Male patient, age 50–59. The patient considered this skin that appeared healthy to them. The patient did not report lesion symptoms. The affected area is the leg. The lesion is described as raised or bumpy. An image taken at a distance. The contributor reports the condition has been present for less than one week. The patient also reports joint pain:
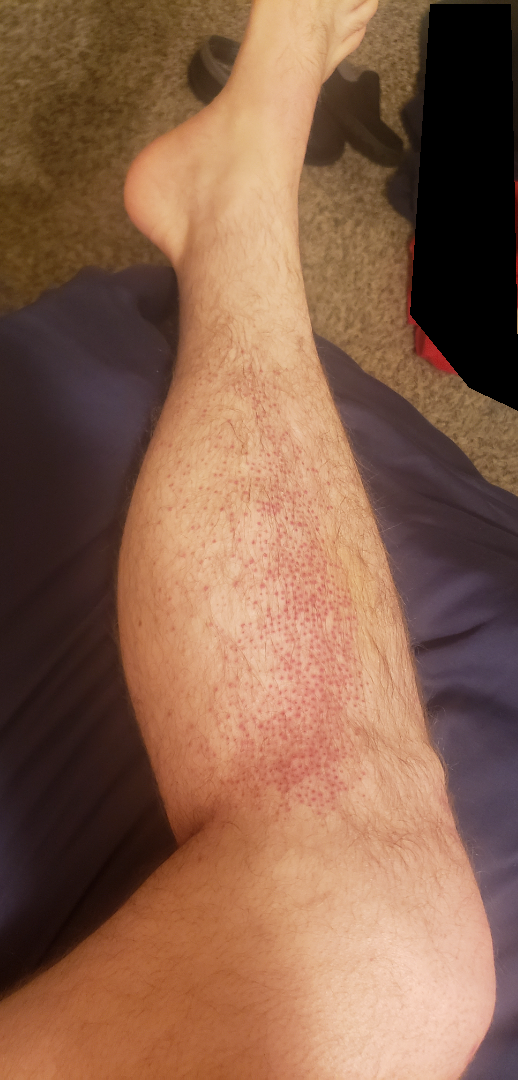assessment = reviewed remotely by three dermatologists: favoring Folliculitis; lower on the differential is Pigmented purpuric eruption; a more distant consideration is Amyloidosis of skin; less probable is Irritant Contact Dermatitis; less likely is Leukocytoclastic Vasculitis; a remote consideration is Pityriasis rubra pilaris; a more distant consideration is Eczema; a remote consideration is scurvy.